A subject age 69 · a smartphone photograph of a skin lesion — 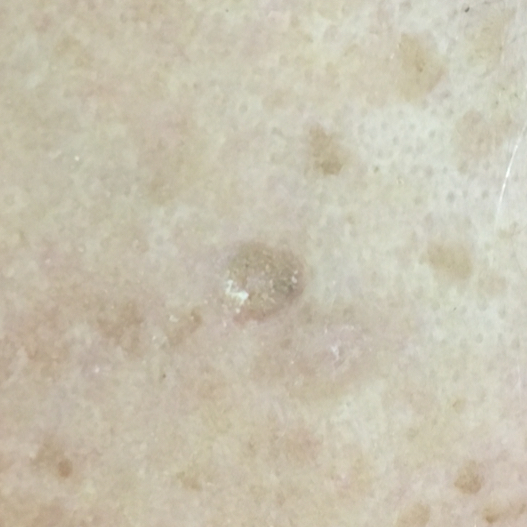The patient describes that the lesion has grown and itches. Diagnosed by dermatologist consensus as a seborrheic keratosis.